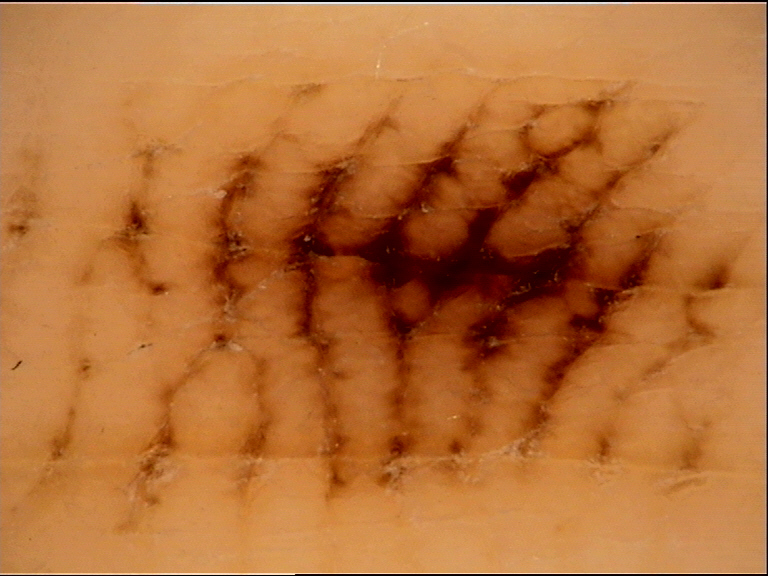Case: A dermoscopic close-up of a skin lesion. Conclusion: The diagnostic label was a banal lesion — an acral junctional nevus.